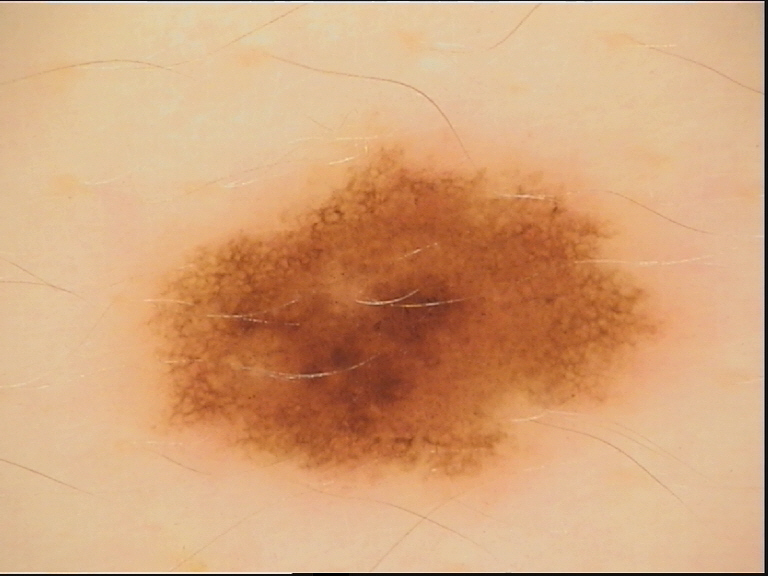assessment — dysplastic junctional nevus (expert consensus)